A subject in their 40s.
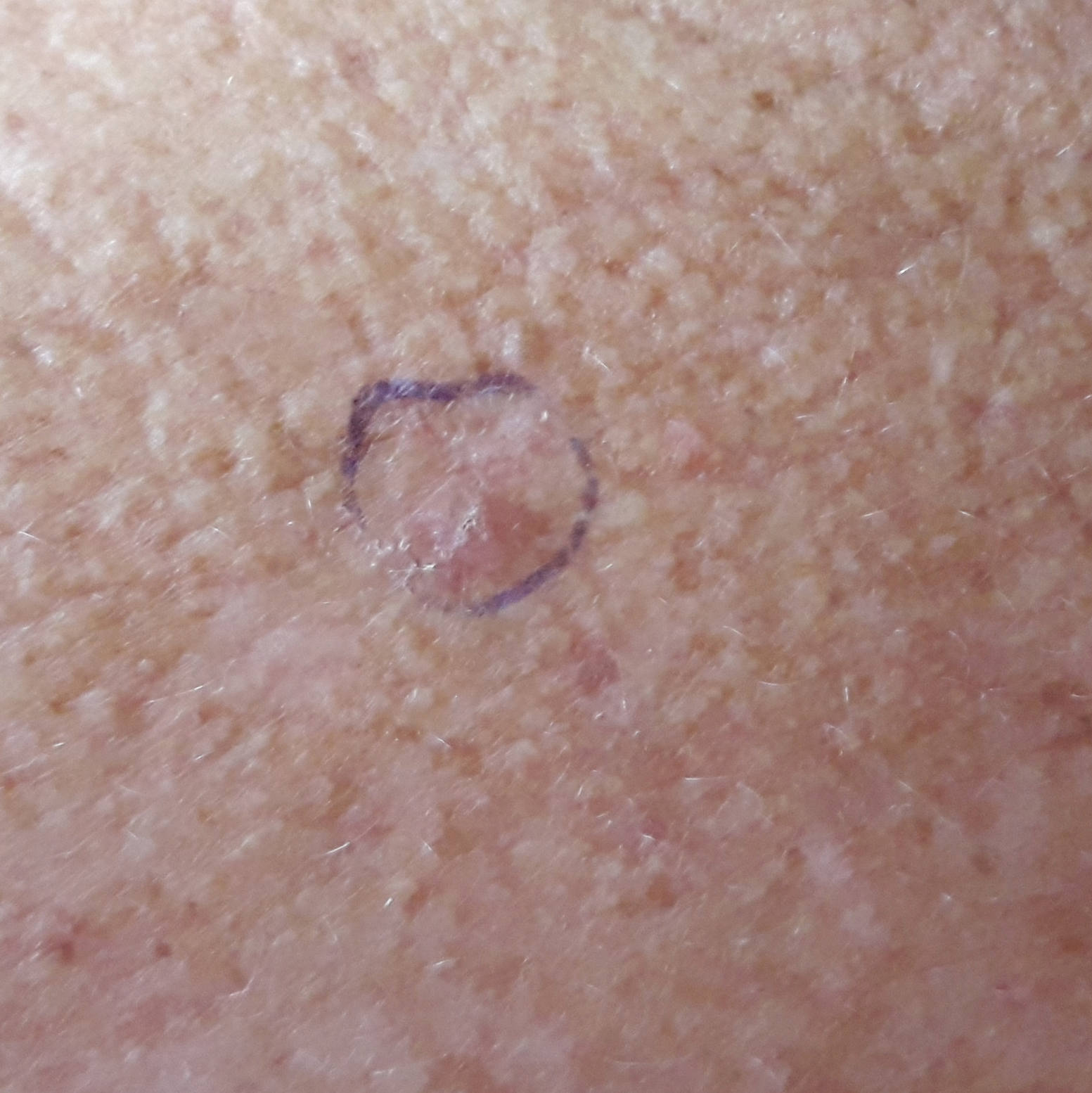| feature | finding |
|---|---|
| anatomic site | the back |
| impression | actinic keratosis (clinical consensus) |